The affected area is the back of the torso. The patient described the issue as a rash. No constitutional symptoms were reported. The photo was captured at a distance — 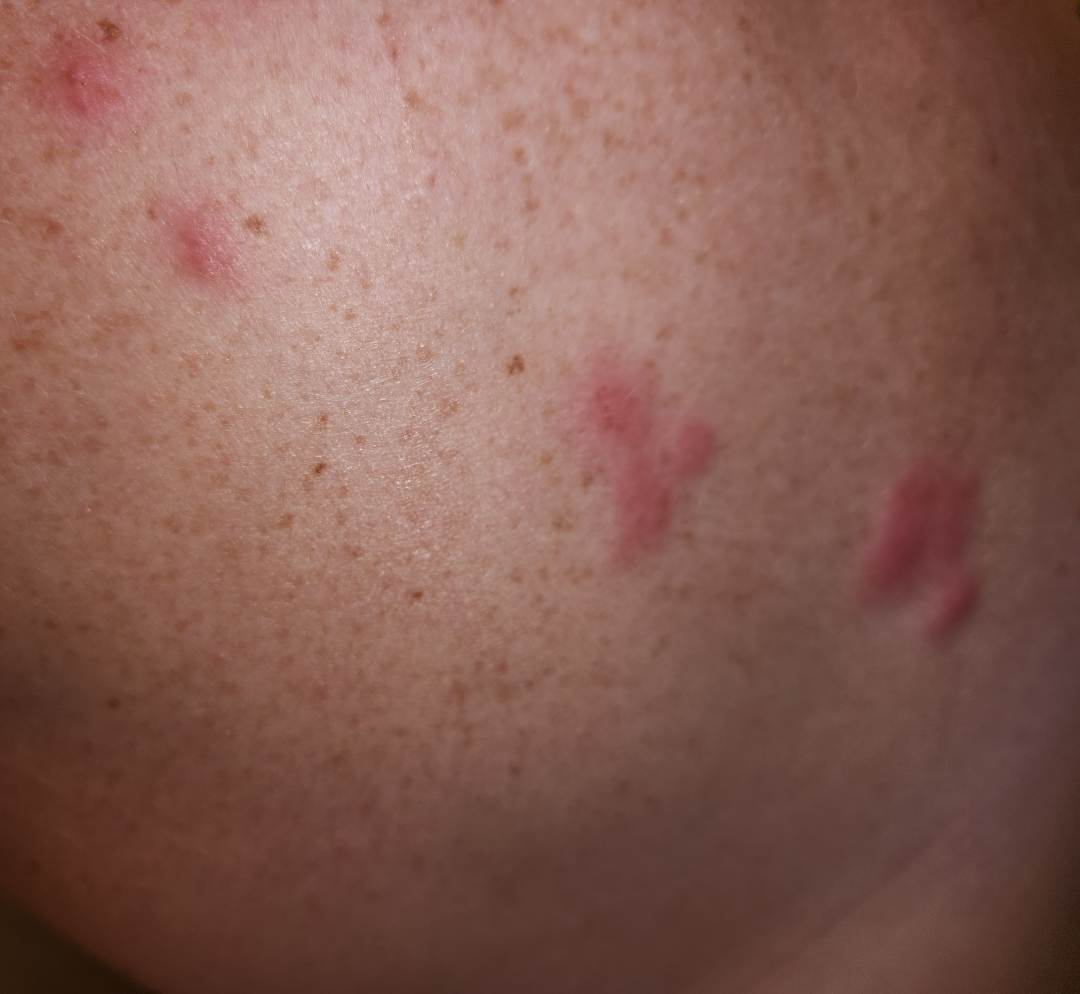assessment: ungradable on photographic review